Dermoscopy of a skin lesion.
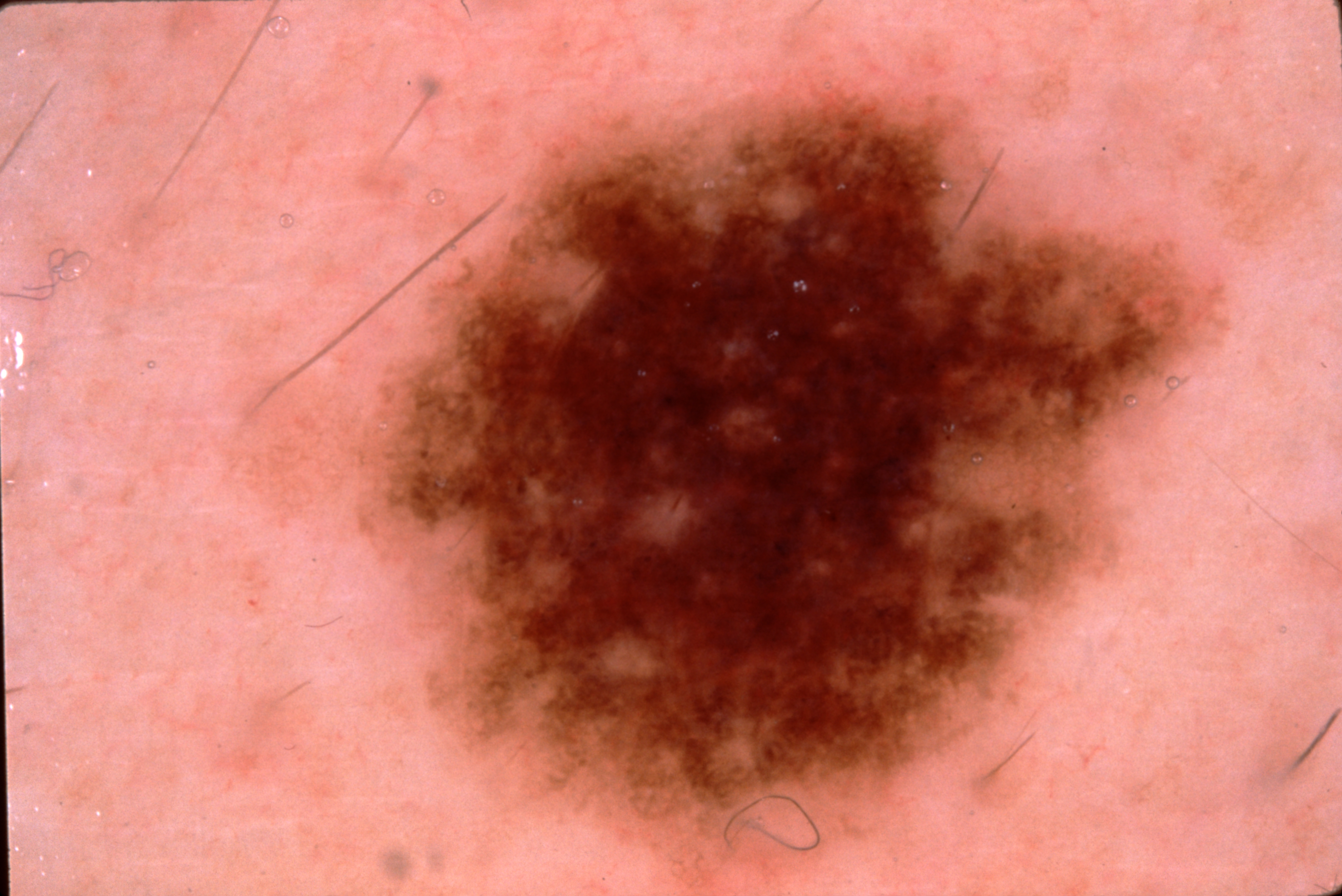lesion bbox=<bbox>348, 79, 1223, 888</bbox> | dermoscopic features=pigment network; absent: streaks, milia-like cysts, and negative network | lesion extent=~37% of the field | impression=a melanocytic nevus, a benign skin lesion.